A dermoscopy image of a single skin lesion: 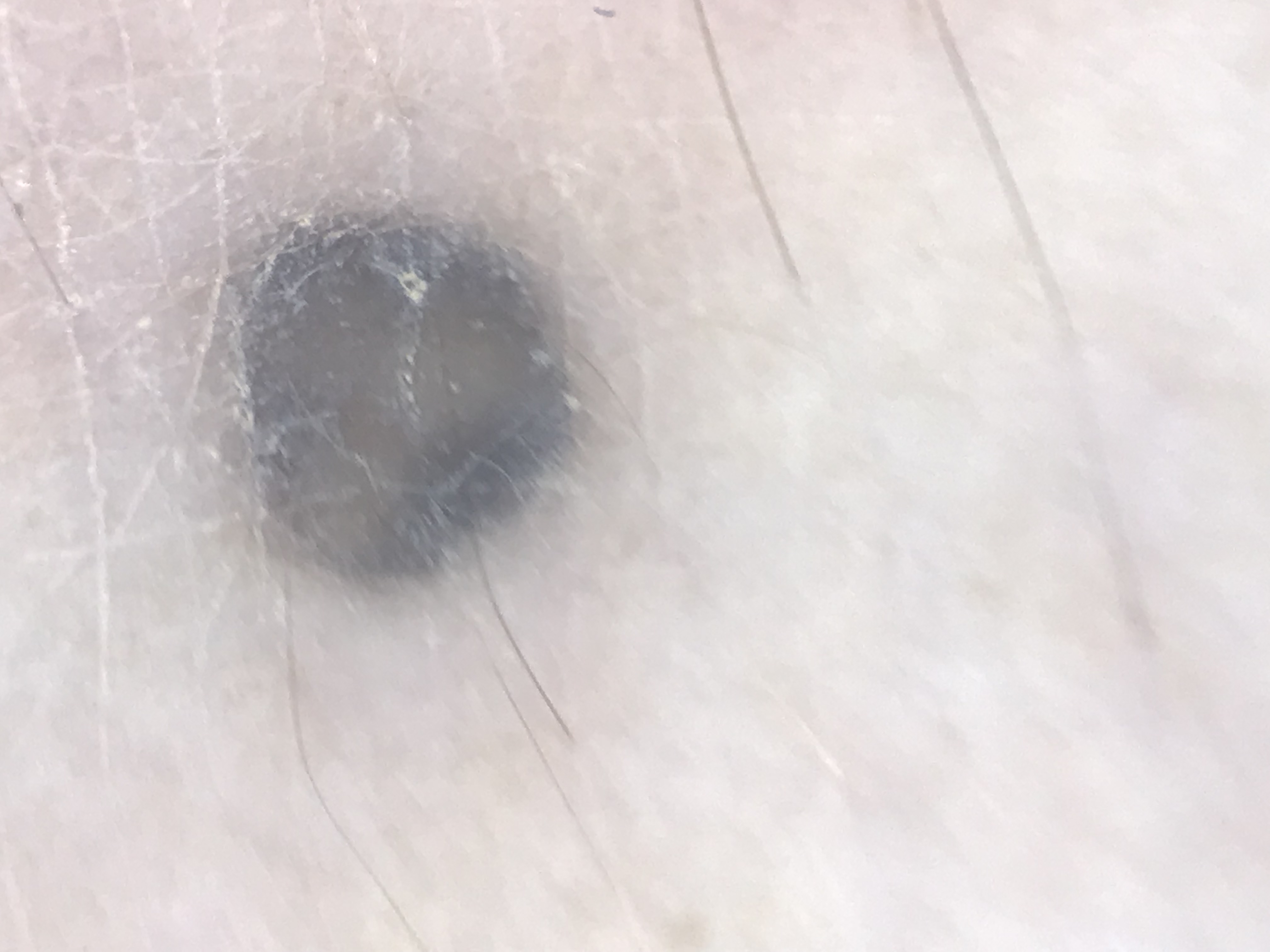The morphology is that of a banal, dermal lesion.
Labeled as a blue nevus.